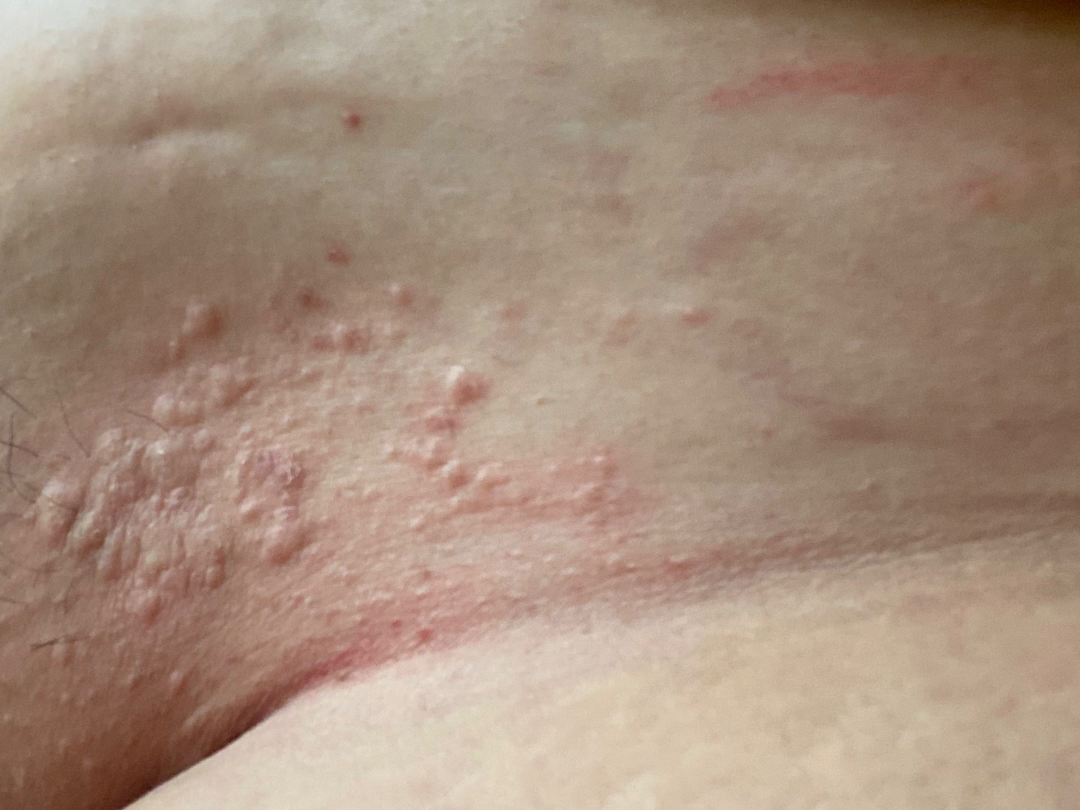assessment — indeterminate from the photograph